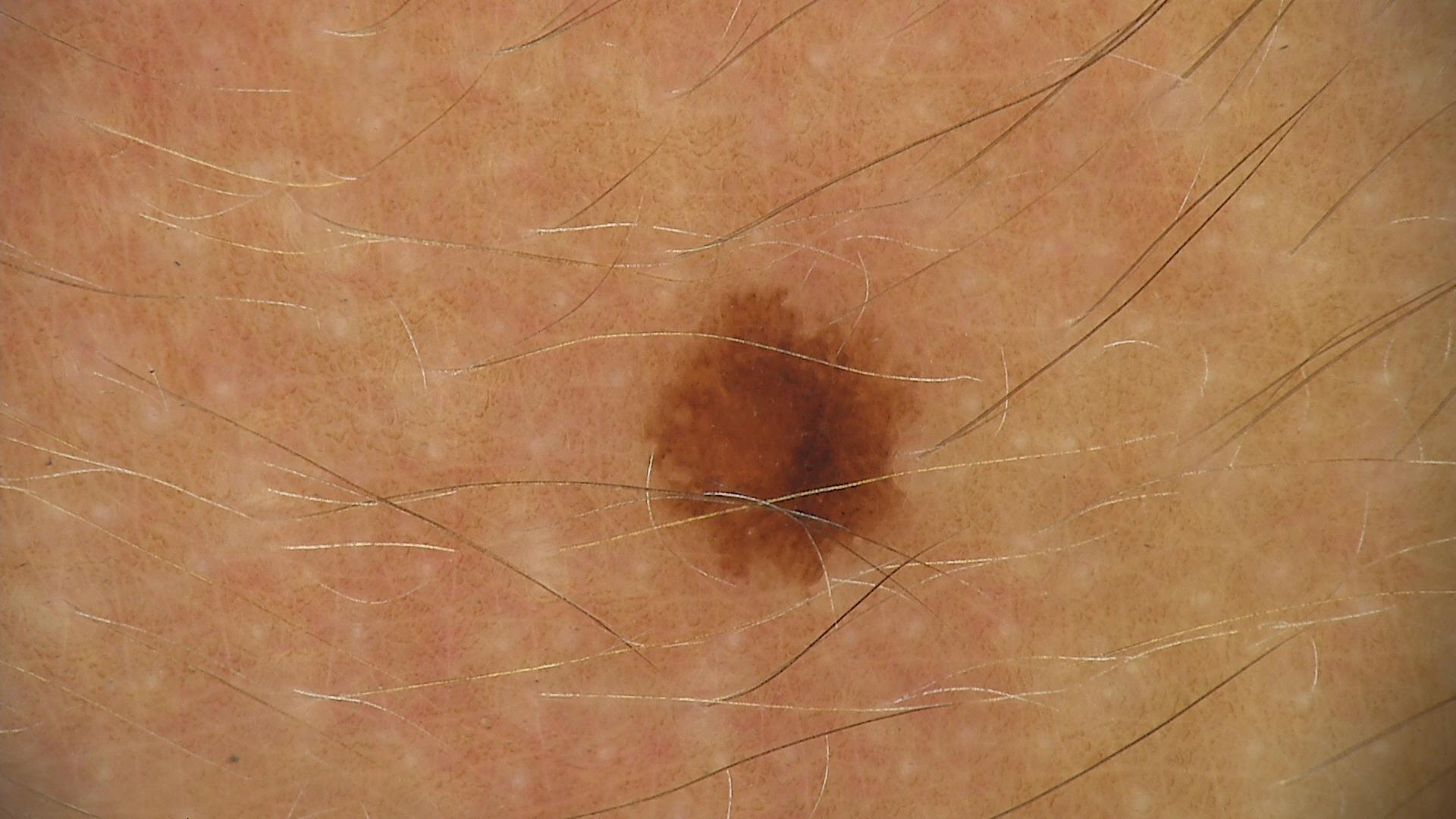diagnosis: dysplastic junctional nevus (expert consensus).